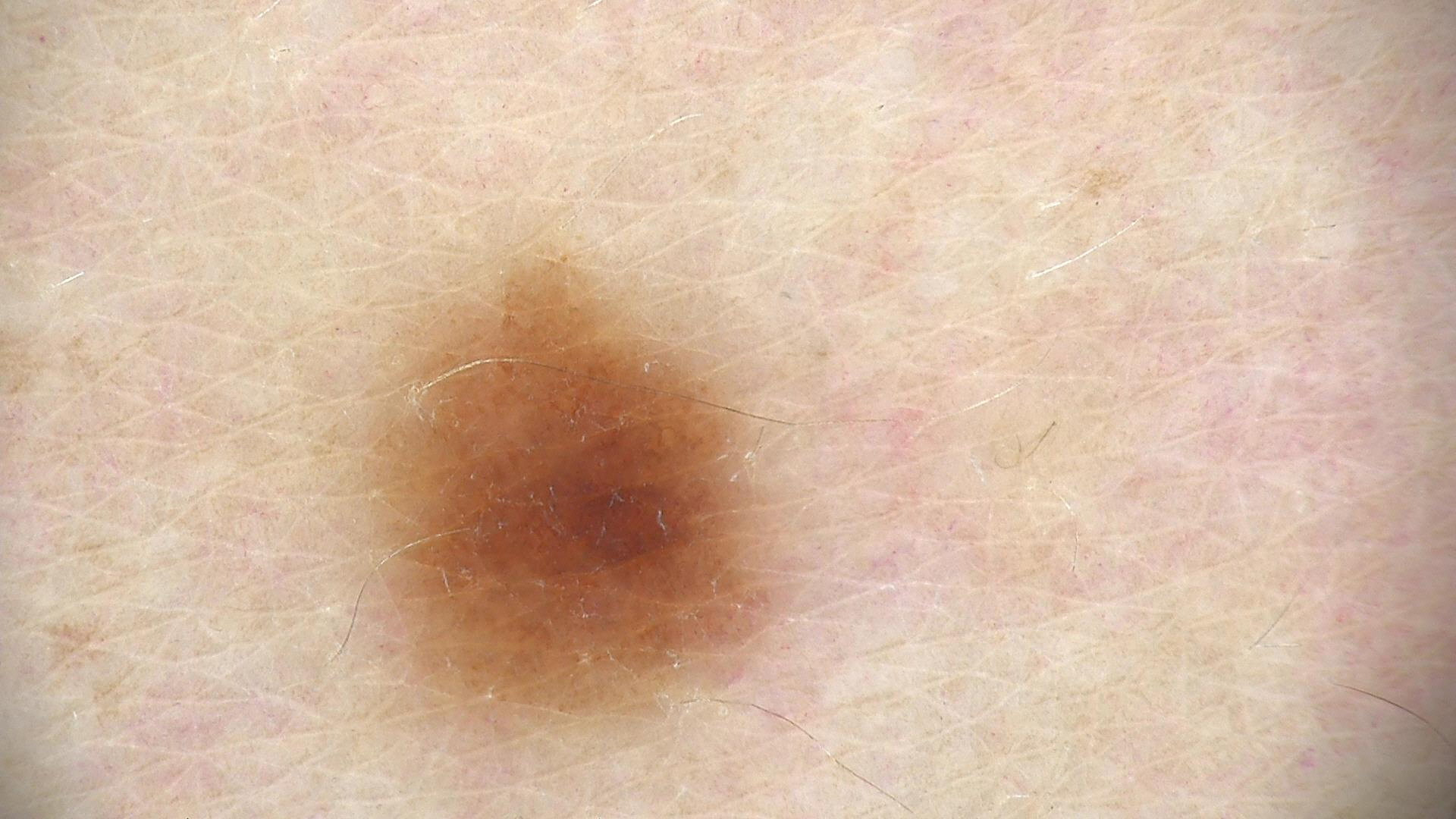class: dysplastic junctional nevus (expert consensus)